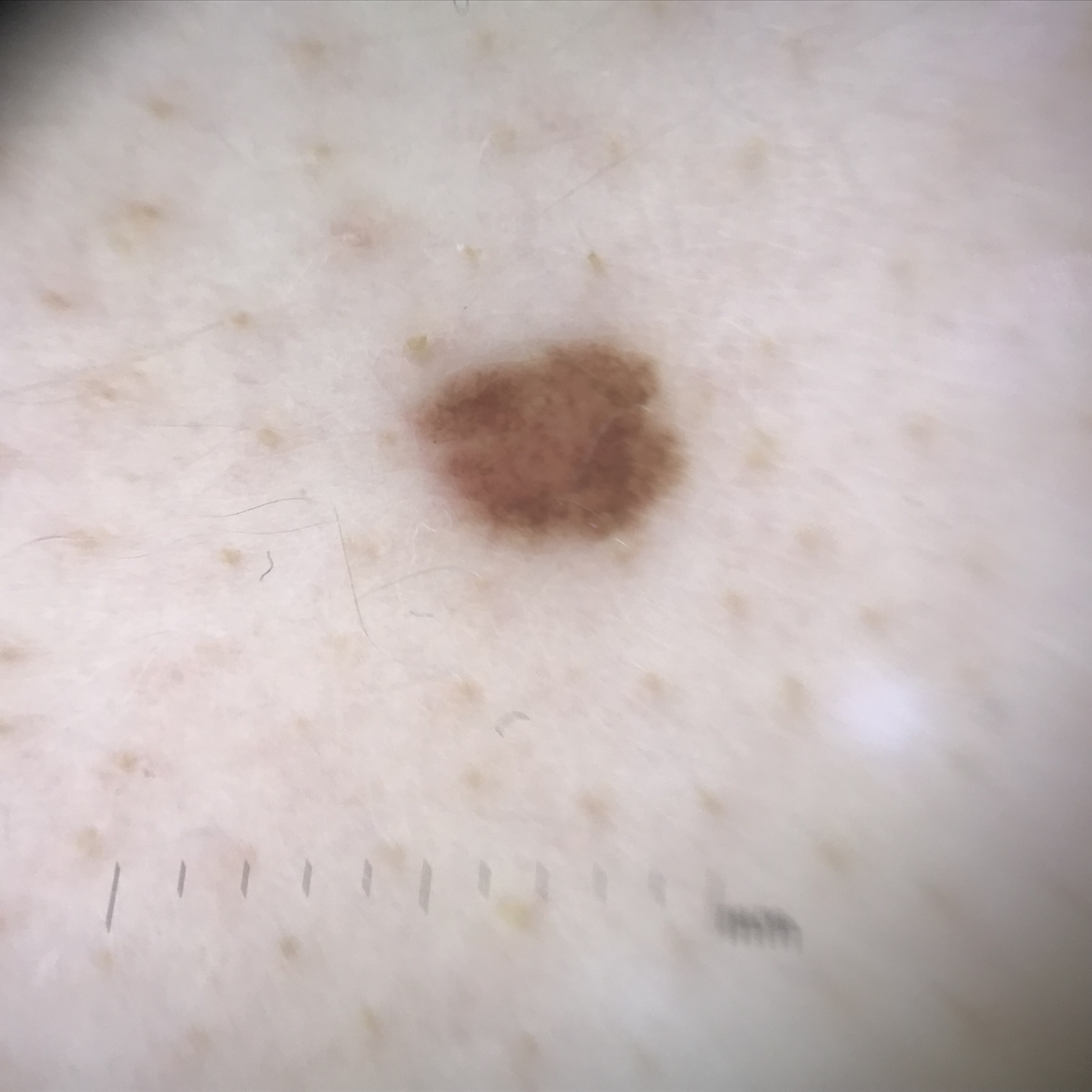{"diagnosis": {"name": "dysplastic junctional nevus", "code": "jd", "malignancy": "benign", "super_class": "melanocytic", "confirmation": "expert consensus"}}